A dermoscopic view of a skin lesion.
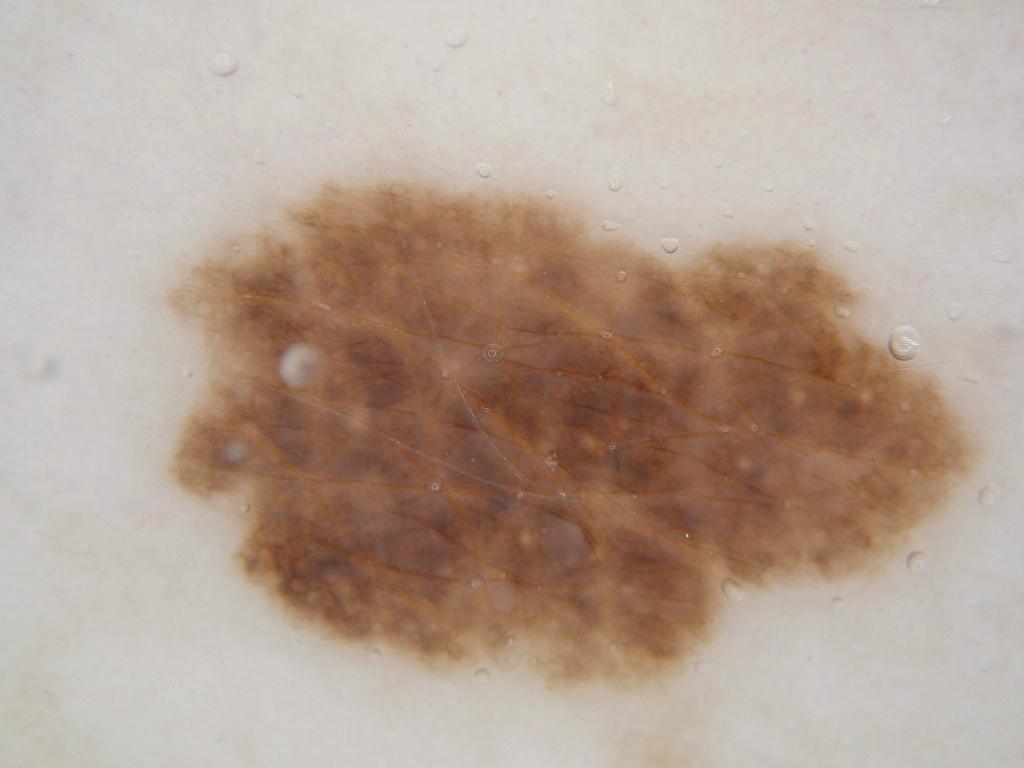The lesion covers approximately 39% of the dermoscopic field. The lesion spans x1=165, y1=177, x2=986, y2=692. Dermoscopically, the lesion shows no streaks, milia-like cysts, pigment network, negative network, or globules. The lesion was assessed as a melanocytic nevus, a benign skin lesion.